A moderate number of moles by the patient's own estimate. By self-report, no personal history of cancer. Referred with a clinical suspicion of melanocytic nevus. A skin lesion imaged with a dermatoscope. The patient says their skin reddens with sun exposure: 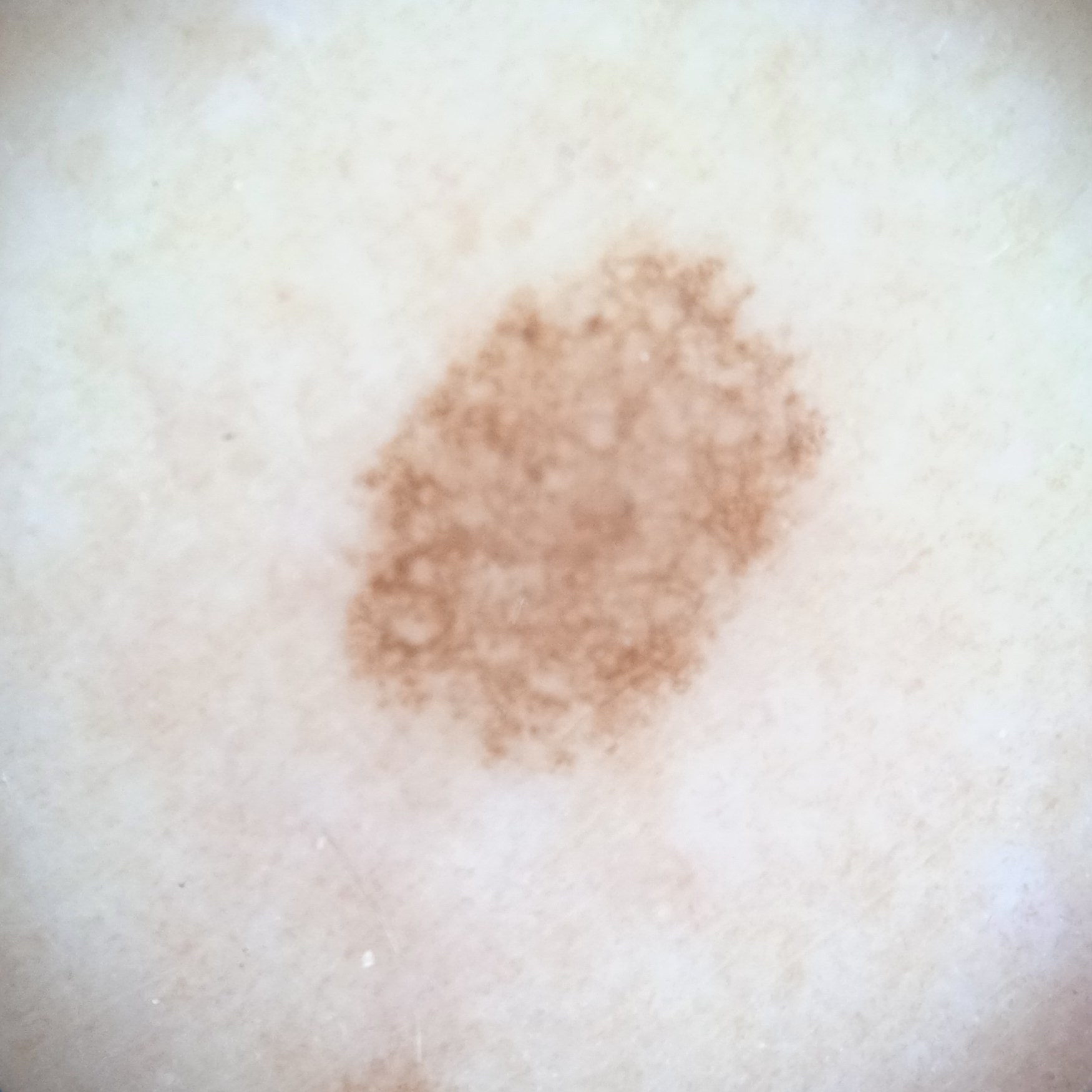Measuring roughly 6.7 mm. The biopsy diagnosis was an atypical (dysplastic) nevus, following excision.